Skin tone: FST V, the arm is involved, the contributor notes the condition has been present for one to three months, self-categorized by the patient as a rash, the patient is a male aged 18–29, this image was taken at an angle: 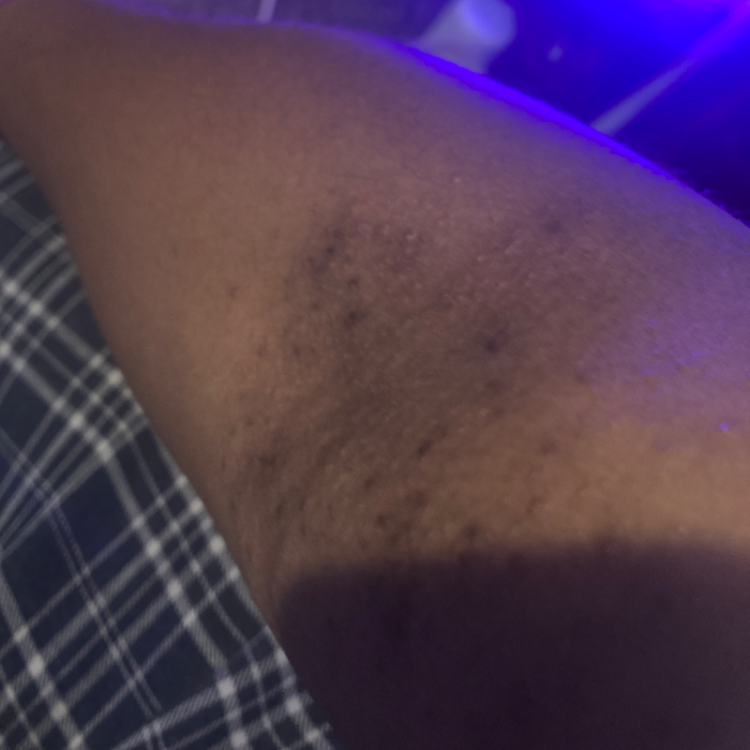Reviewed remotely by one dermatologist: in keeping with Eczema.